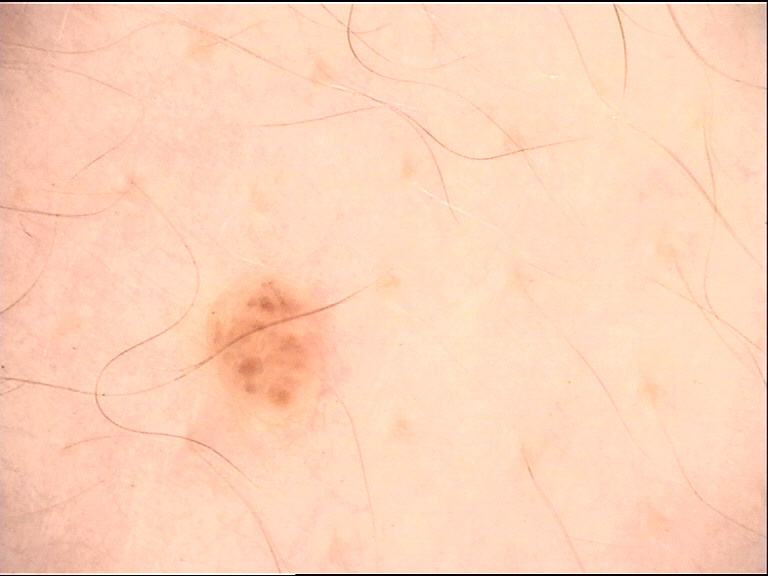imaging — dermoscopy | classification — banal | diagnosis — compound nevus (expert consensus).